Dermoscopy of a skin lesion:
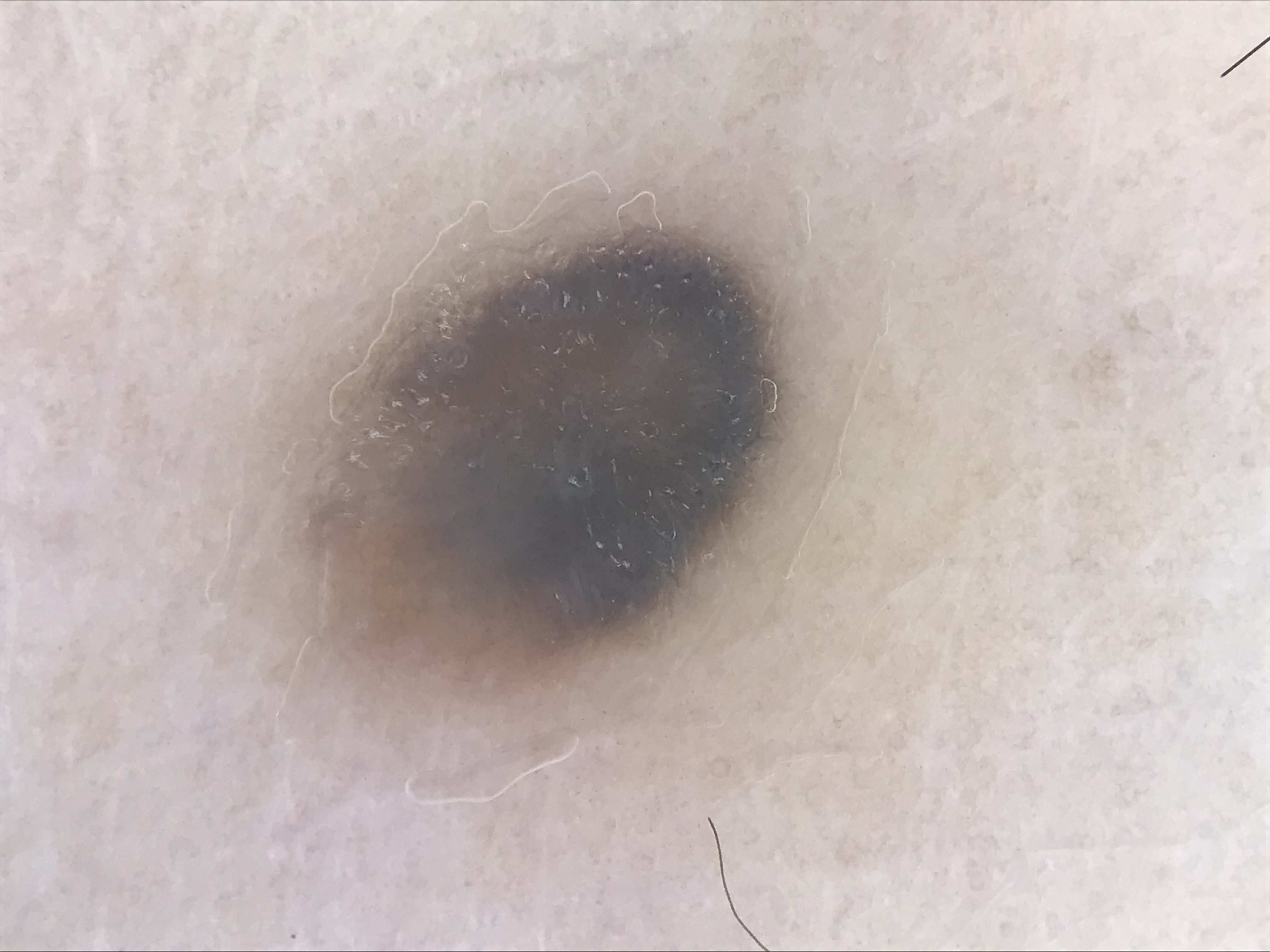label: blue nevus (expert consensus).